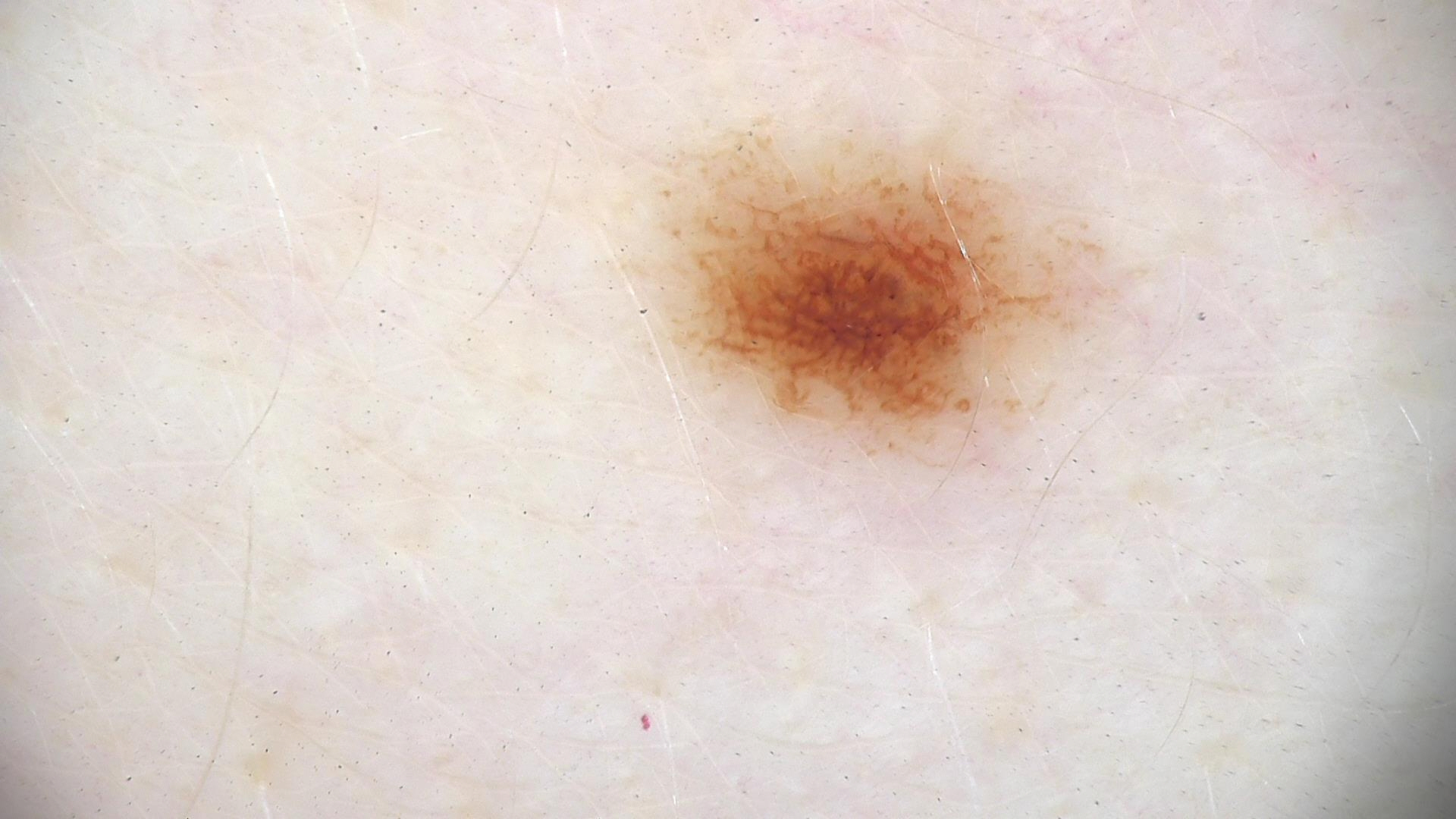Findings:
A dermoscopic image of a skin lesion.
Impression:
Classified as a dysplastic junctional nevus.